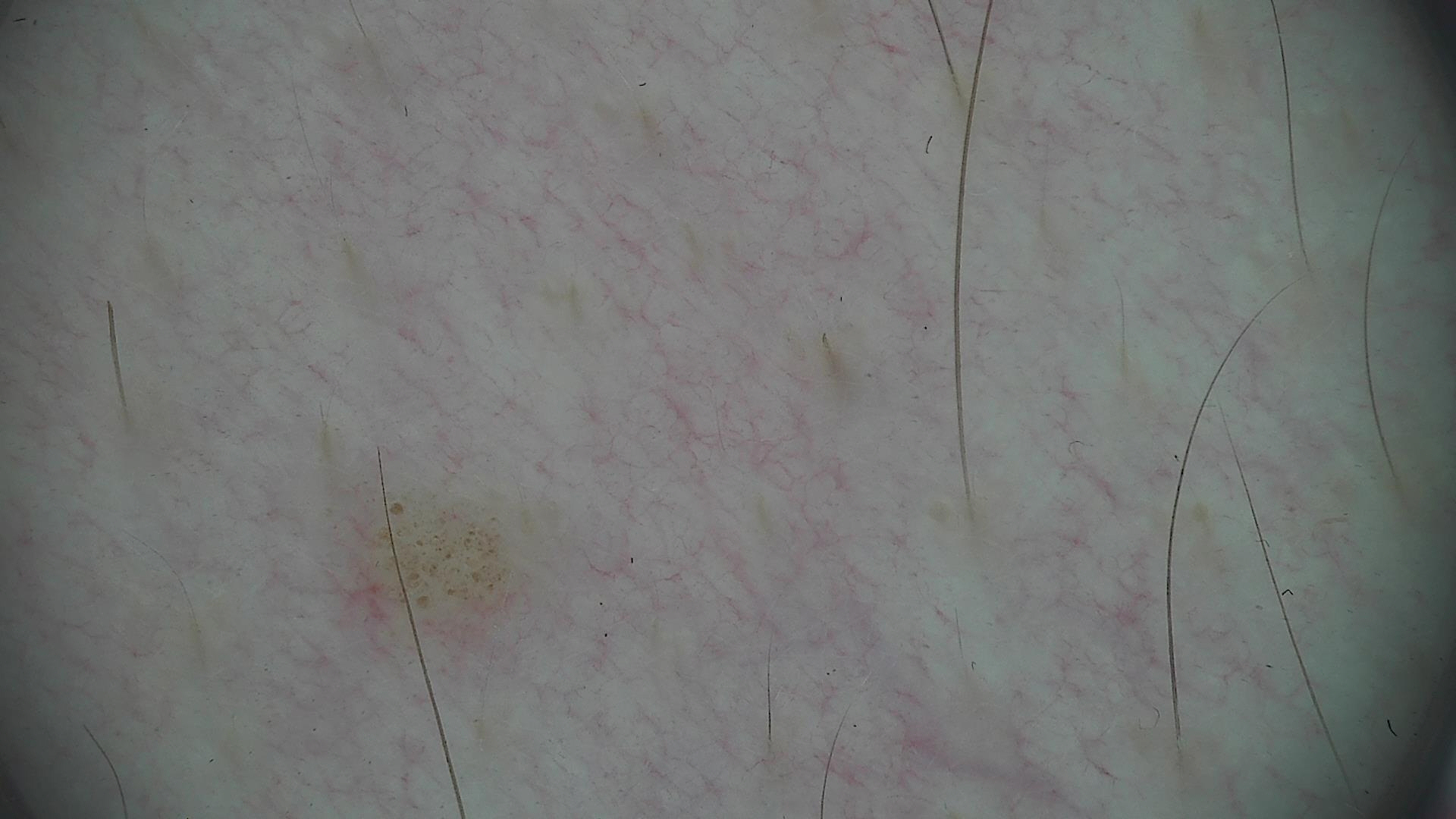modality — dermatoscopy
label — junctional nevus (expert consensus)